A male subject roughly 40 years of age; dermoscopy of a skin lesion: 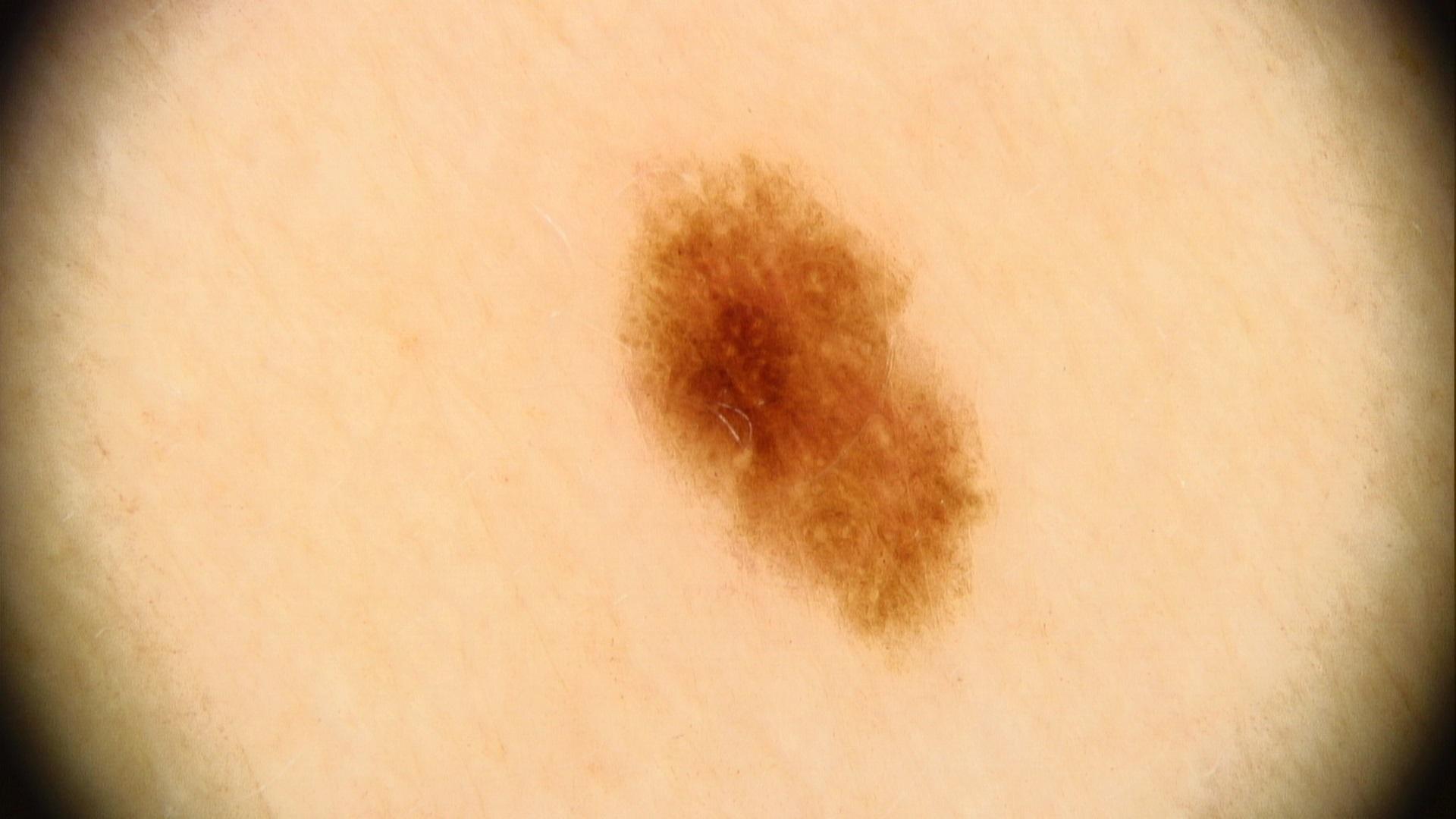Summary:
Located on the trunk, specifically the anterior trunk.
Conclusion:
Expert review favored a nevus.